A dermoscopic image of a skin lesion.
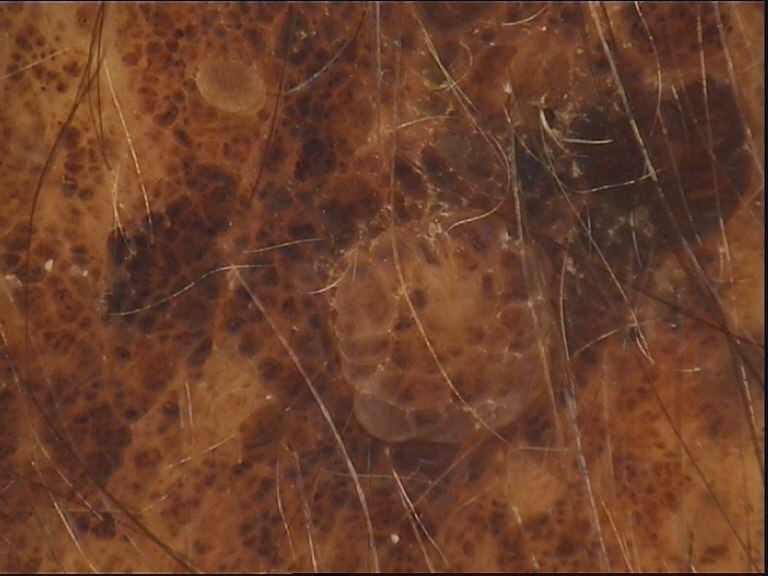Diagnosed as a banal lesion — a congenital compound nevus.